A dermoscopic close-up of a skin lesion:
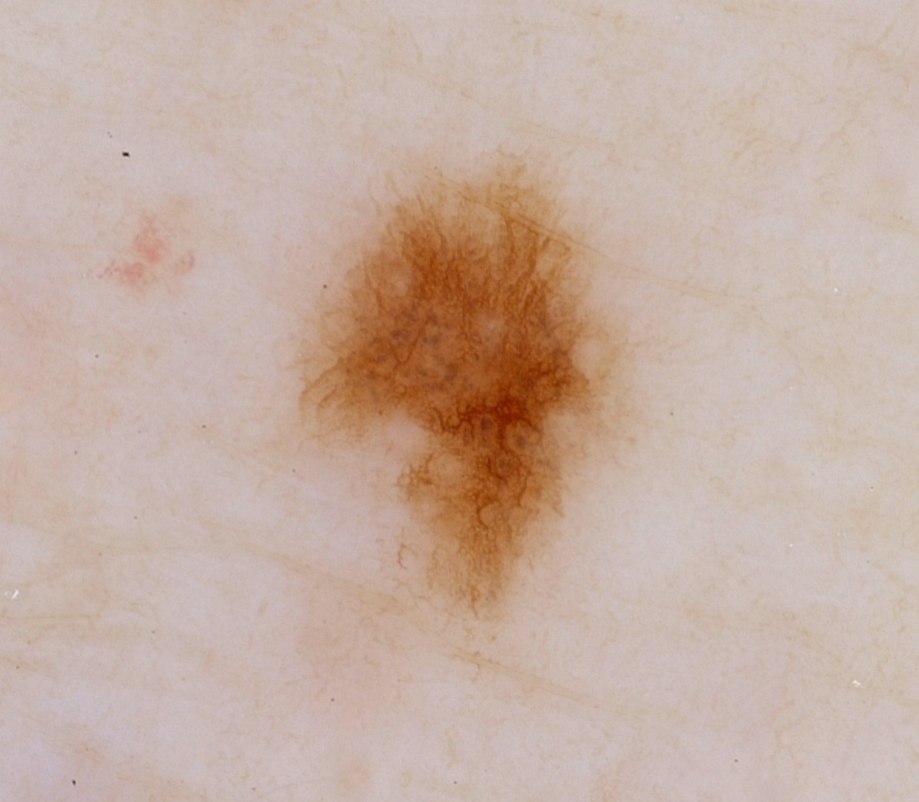  lesion_location:
    bbox_xyxy:
      - 296
      - 164
      - 621
      - 617
  dermoscopic_features:
    present:
      - pigment network
    absent:
      - streaks
      - negative network
      - milia-like cysts
      - globules
  lesion_extent:
    approx_field_fraction_pct: 13
  diagnosis:
    name: melanocytic nevus
    malignancy: benign
    lineage: melanocytic
    provenance: clinical